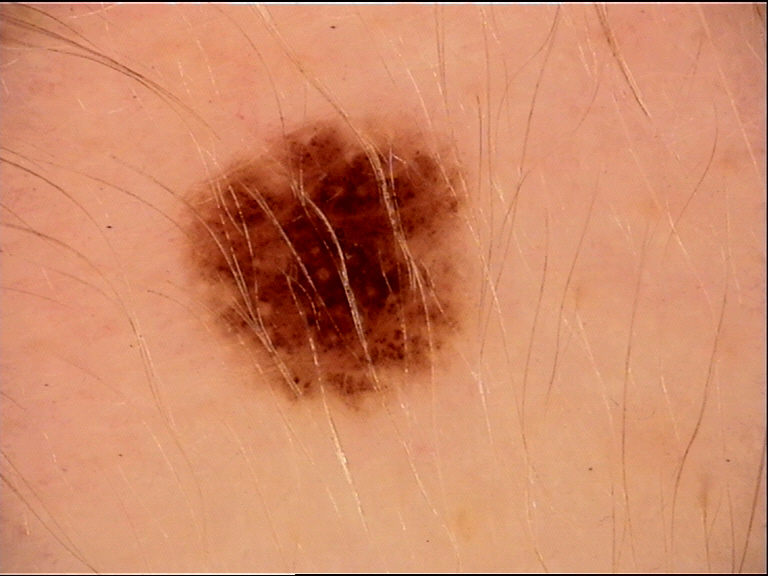Q: What is this lesion?
A: dysplastic junctional nevus (expert consensus)